The affected area is the leg. Symptoms reported: darkening and itching. The photograph is a close-up of the affected area. The contributor reports the lesion is raised or bumpy. Present for less than one week. Self-categorized by the patient as a rash — 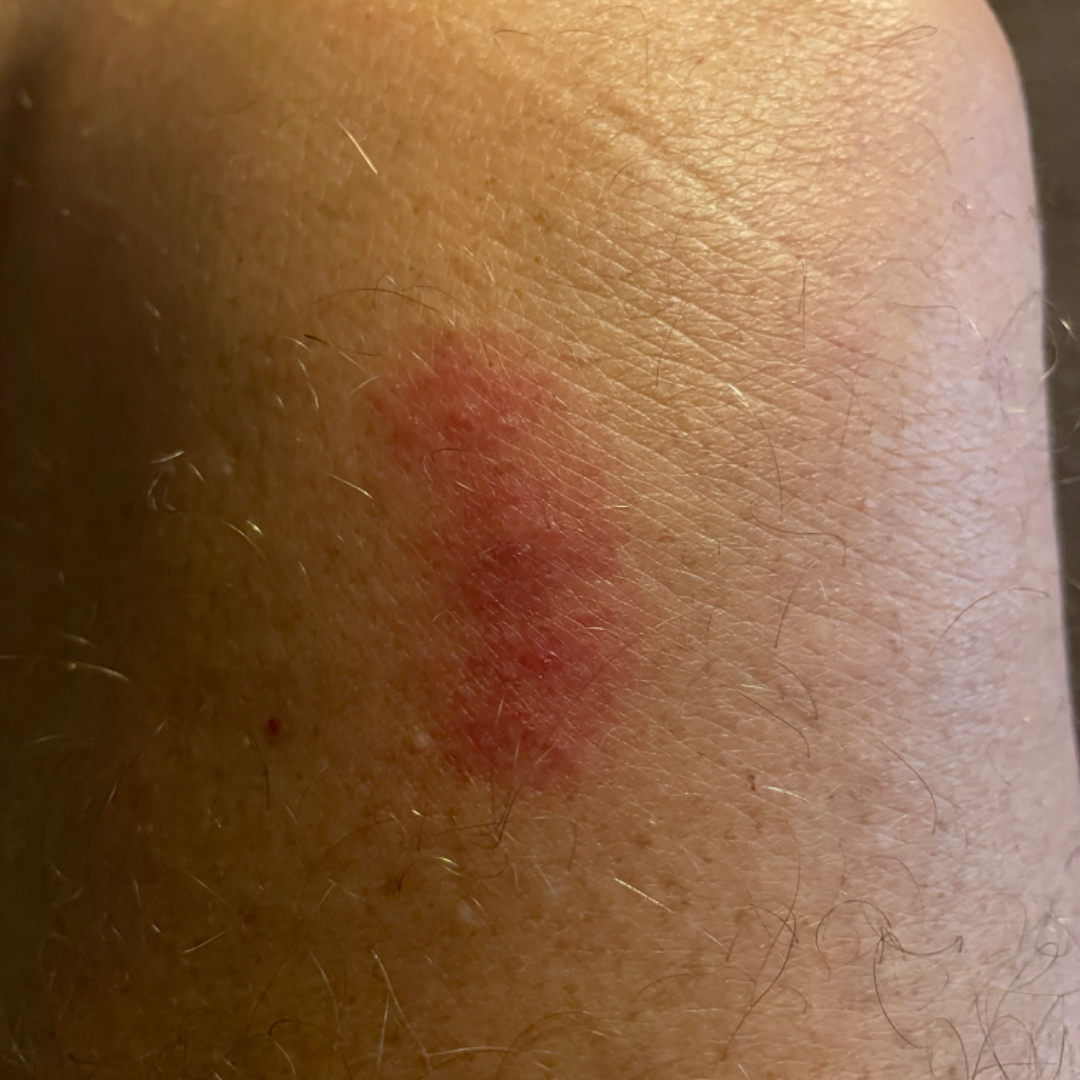On dermatologist assessment of the image: Eczema (primary); Hypersensitivity (considered).